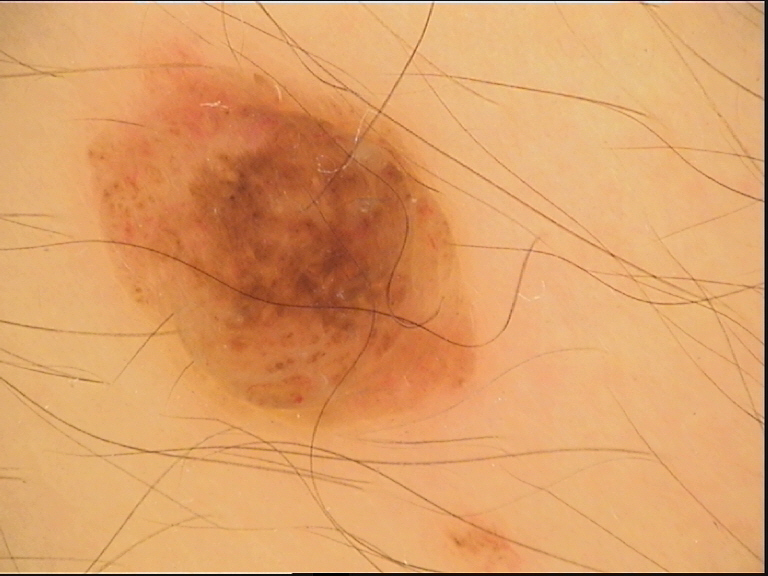modality: dermatoscopy, diagnostic label: compound nevus (expert consensus).